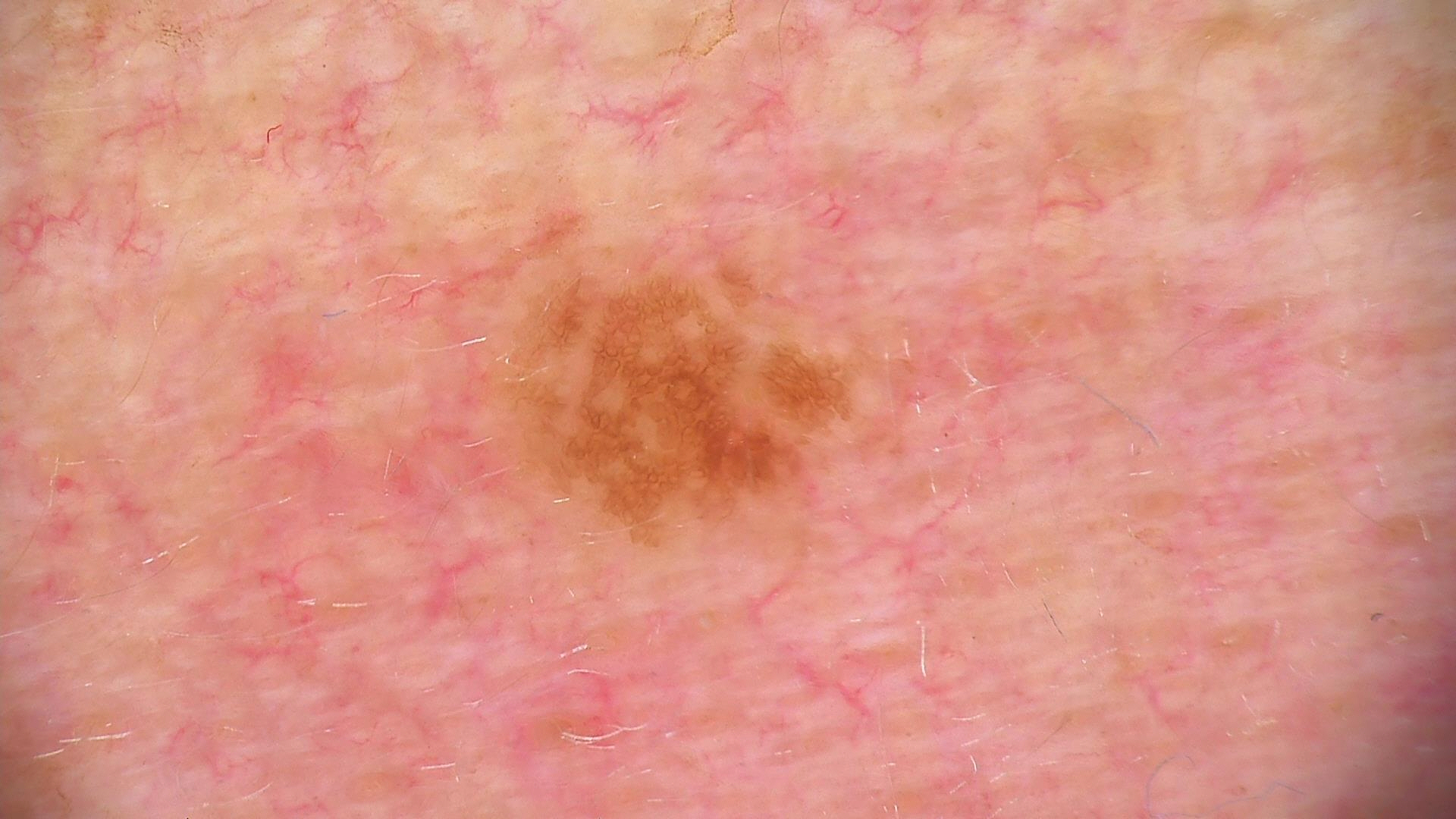modality = dermatoscopy
subtype = banal
diagnostic label = compound nevus (expert consensus)